This image was taken at a distance.
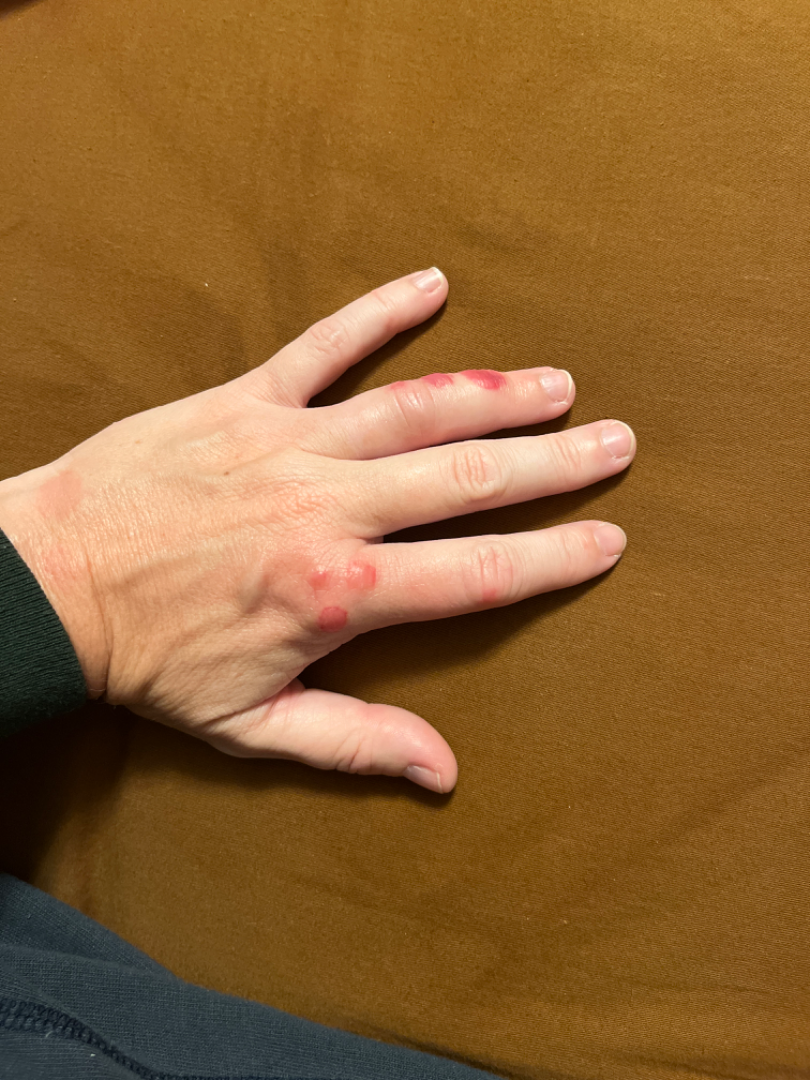The reviewing dermatologist was unable to assign a differential diagnosis from the image. Reported duration is about one day. Associated systemic symptoms include joint pain and fatigue. The patient notes itching, pain and burning.